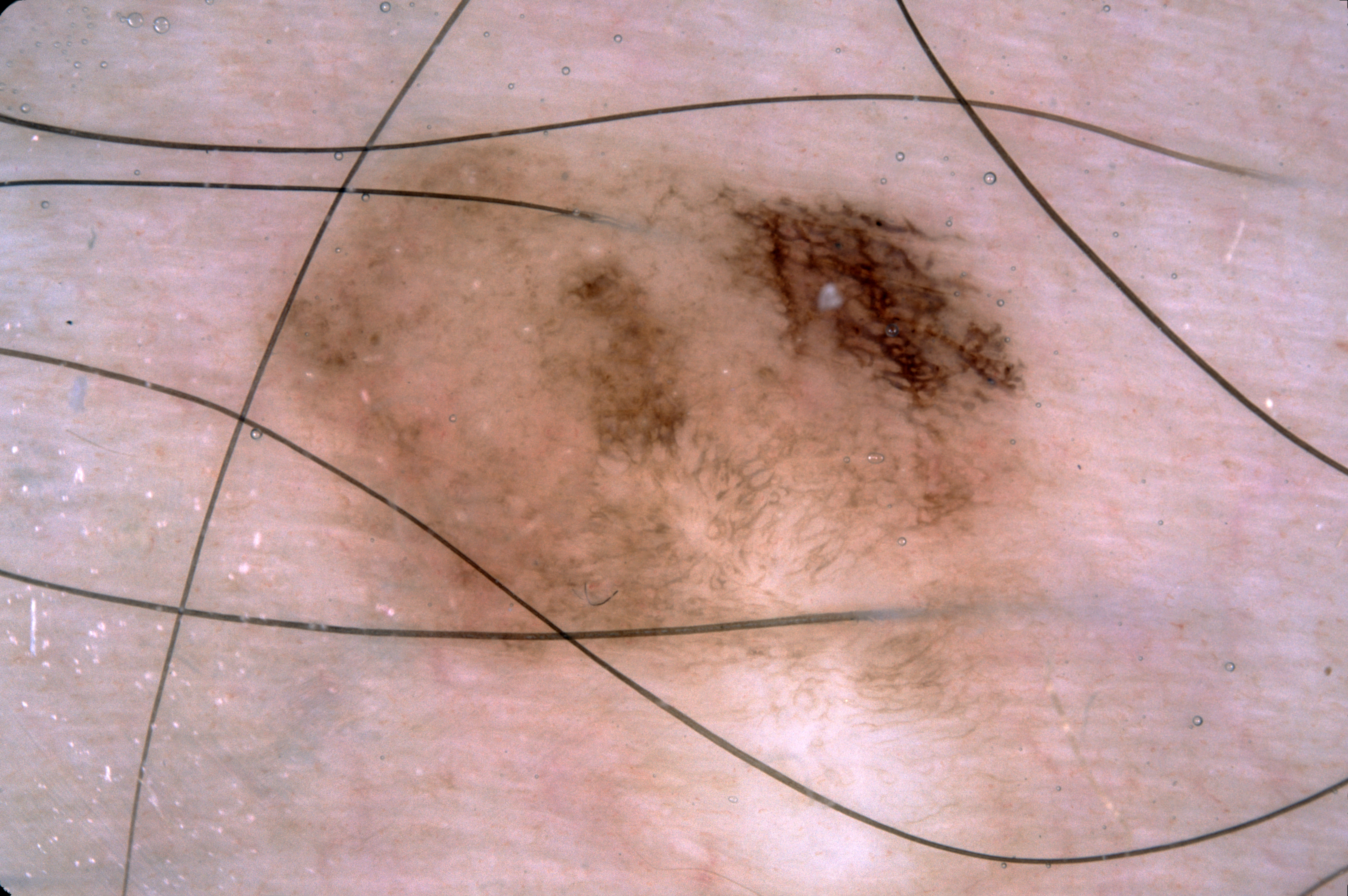<record>
<image>
  <modality>dermoscopy</modality>
</image>
<lesion_location>
  <bbox_xyxy>254, 112, 1118, 756</bbox_xyxy>
</lesion_location>
<dermoscopic_features>
  <present>pigment network</present>
  <absent>negative network, streaks, milia-like cysts</absent>
</dermoscopic_features>
<diagnosis>
  <name>melanocytic nevus</name>
  <malignancy>benign</malignancy>
  <lineage>melanocytic</lineage>
  <provenance>clinical</provenance>
</diagnosis>
</record>